The patient was assessed as skin type II; the chart records alcohol use, prior malignancy (patient or family), pesticide exposure, and no tobacco use; a clinical photo of a skin lesion taken with a smartphone.
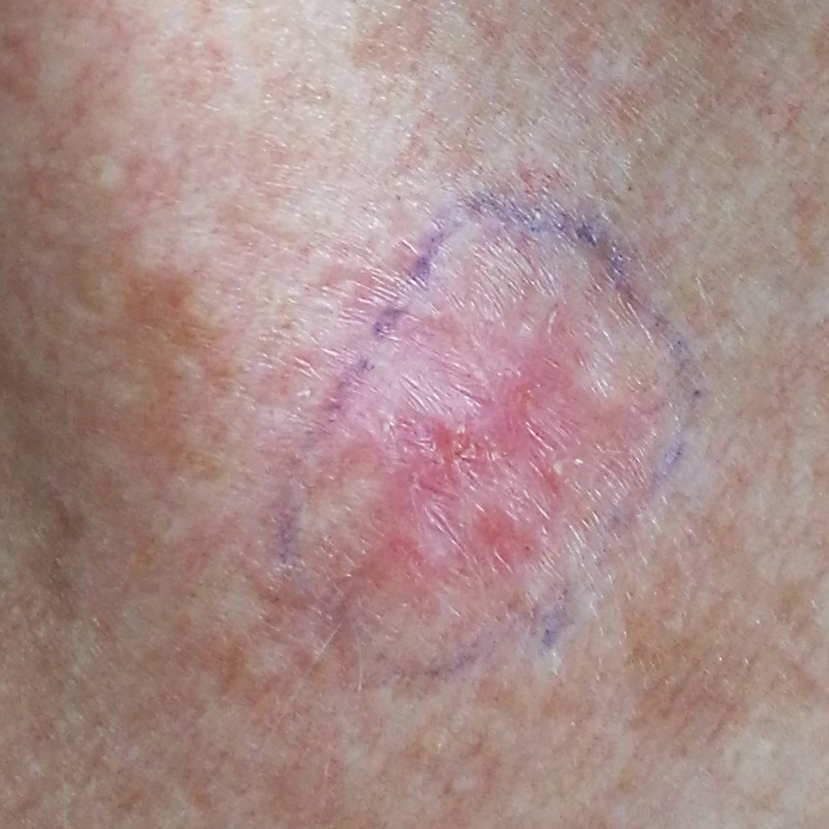Summary: The lesion involves the chest. Measuring about 10 × 8 mm. By the patient's account, the lesion itches, is elevated, has bled, and has grown. Pathology: On biopsy, the diagnosis was a basal cell carcinoma.